This image was taken at a distance. Female contributor, age 30–39. Located on the leg:
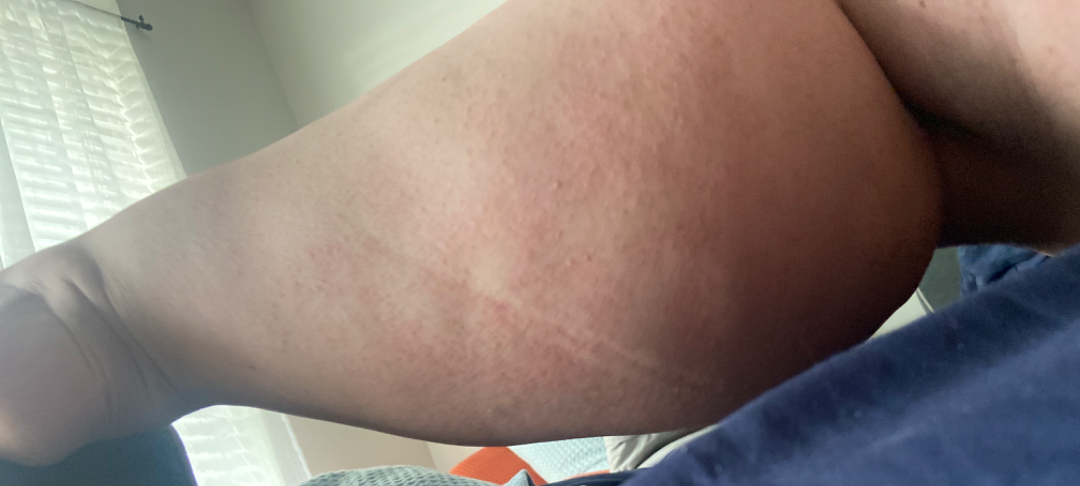Background: The condition has been present for less than one week. The contributor notes bothersome appearance and itching. The patient considered this a rash. Findings: The reviewing panel's impression was: most likely Keratosis pilaris; also on the differential is Eczema; less probable is Miliaria; a more distant consideration is Folliculitis.